The patient was assessed as Fitzpatrick skin type I; a dermoscopic photograph of a skin lesion; a male patient aged 73-77: 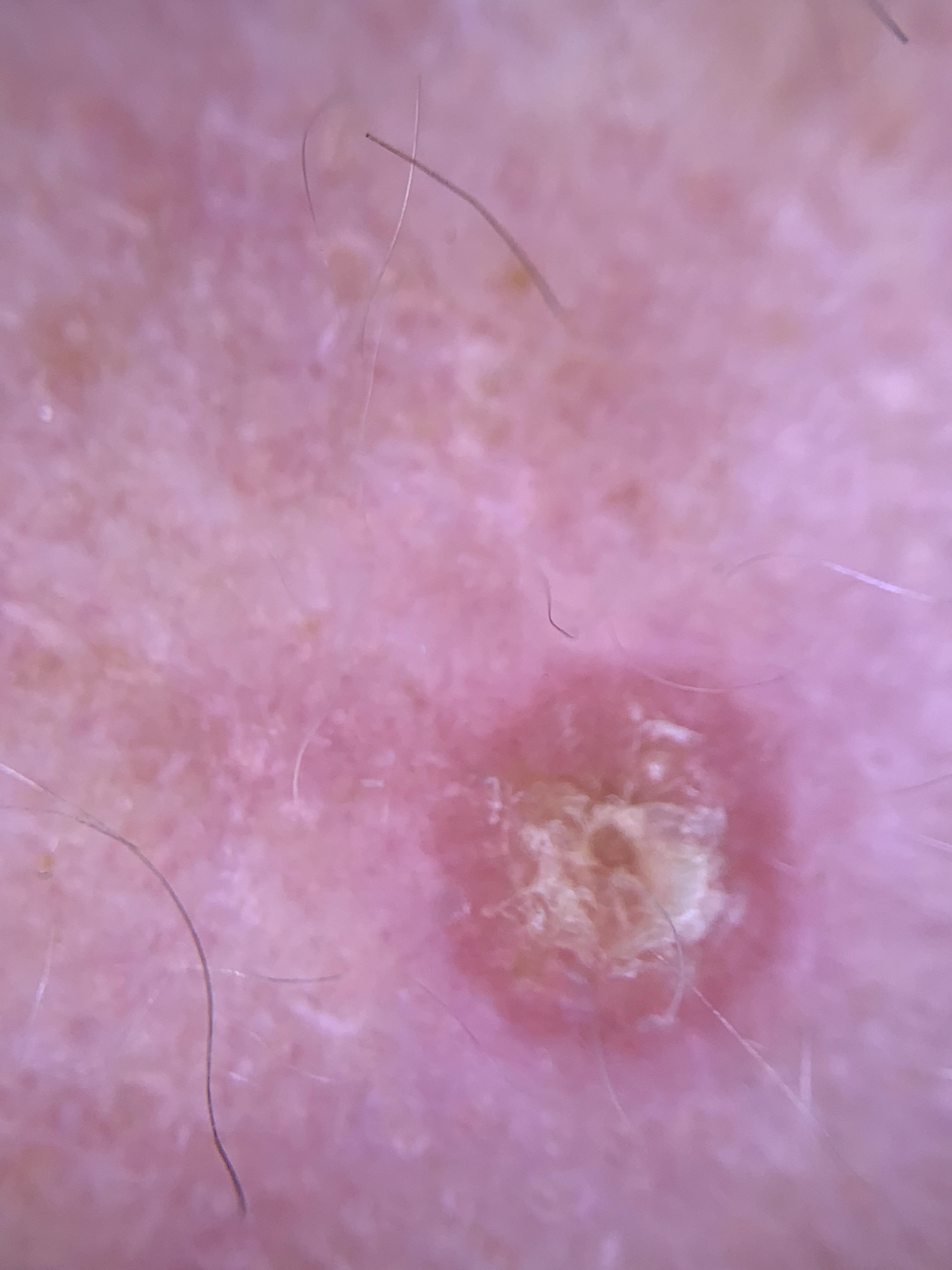The lesion was found on the head or neck.
Expert review favored a premalignant, epidermal lesion — a solar or actinic keratosis.